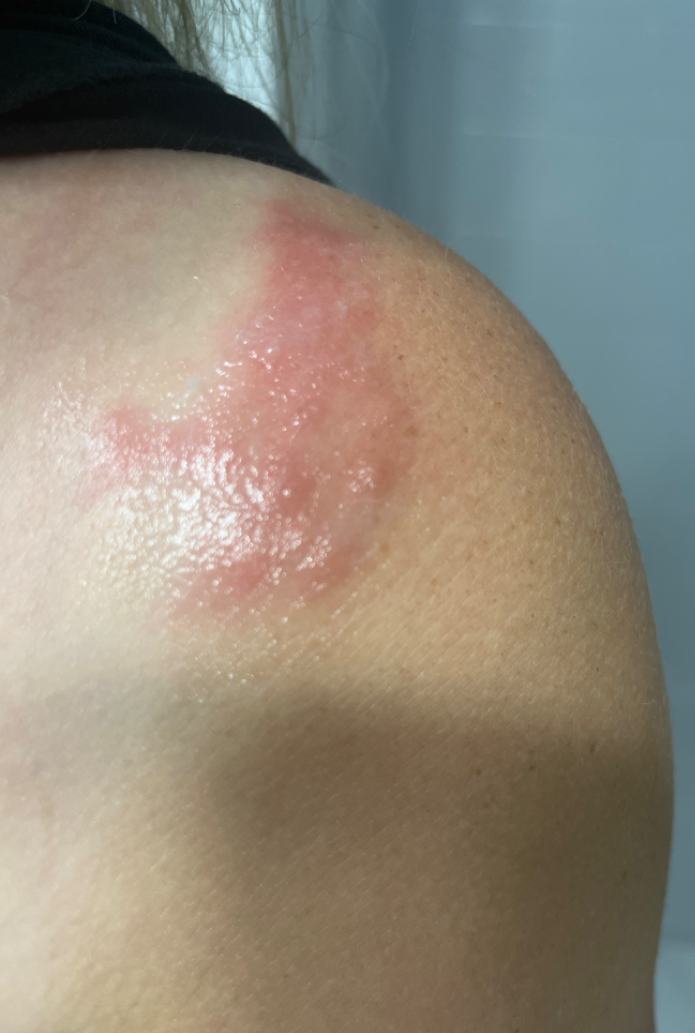History:
The patient considered this a rash. The lesion is described as raised or bumpy. Female patient, age 30–39. A close-up photograph. Reported lesion symptoms include bothersome appearance, itching and pain. The patient reported no systemic symptoms.
Impression:
The reviewing clinician's impression was: the favored diagnosis is Allergic Contact Dermatitis; an alternative is Insect Bite; the differential also includes Herpes Zoster.